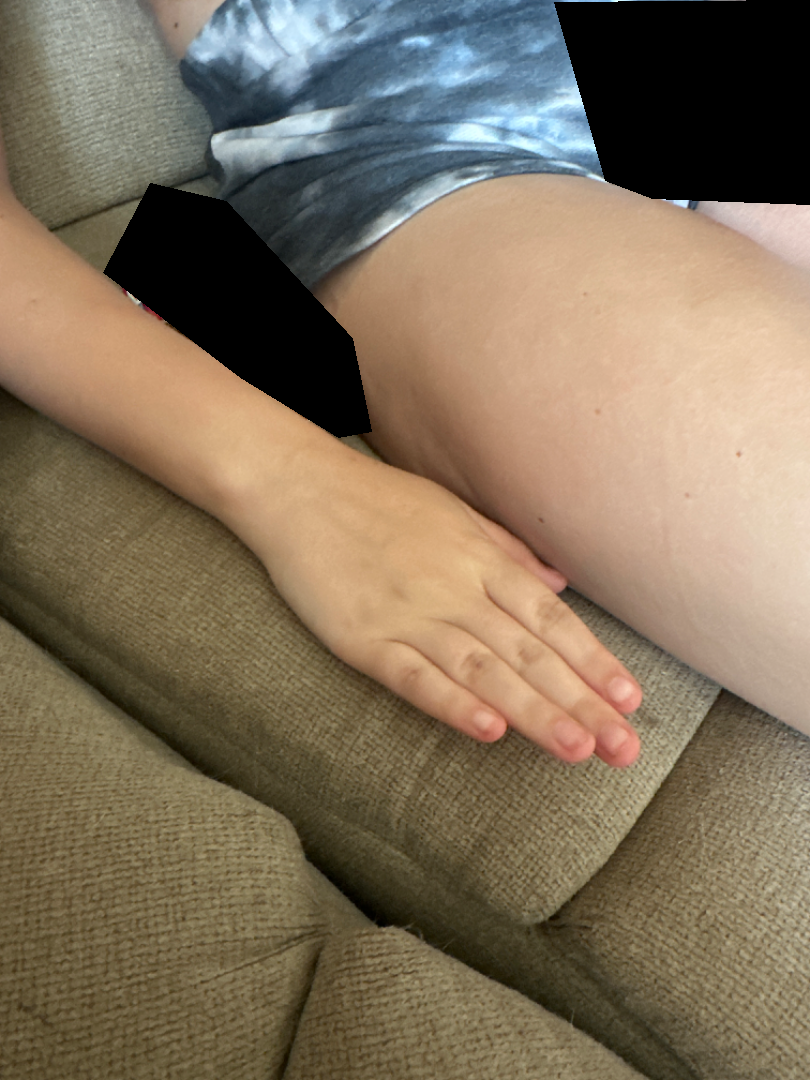No discernible pathology was noted by the reviewing dermatologist.
An image taken at a distance.
Lay reviewers estimated MST 2 or 4.